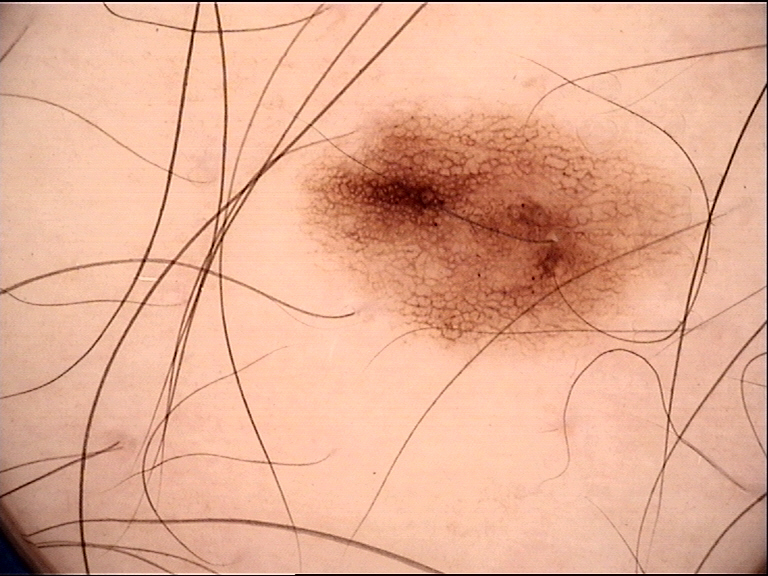The diagnosis was a dysplastic junctional nevus.